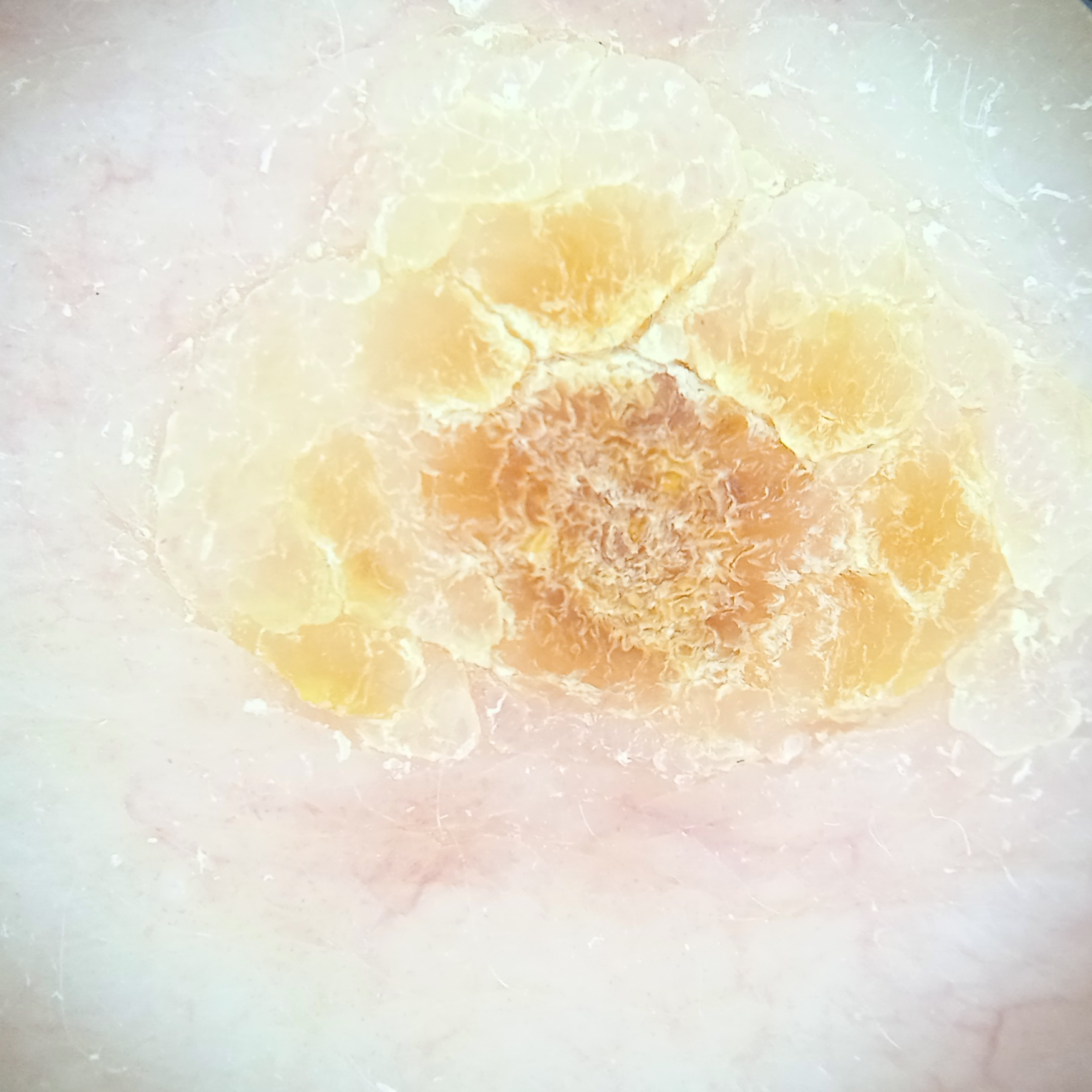Case summary: A skin lesion imaged with a dermatoscope. A male subject 77 years of age. Imaged for a research study, with no referral diagnosis recorded. The lesion is on the back. Measuring roughly 11.1 mm. Impression: Dermatologist review favored an actinic keratosis.